Close-up view; male subject, age 30–39; the leg is involved:
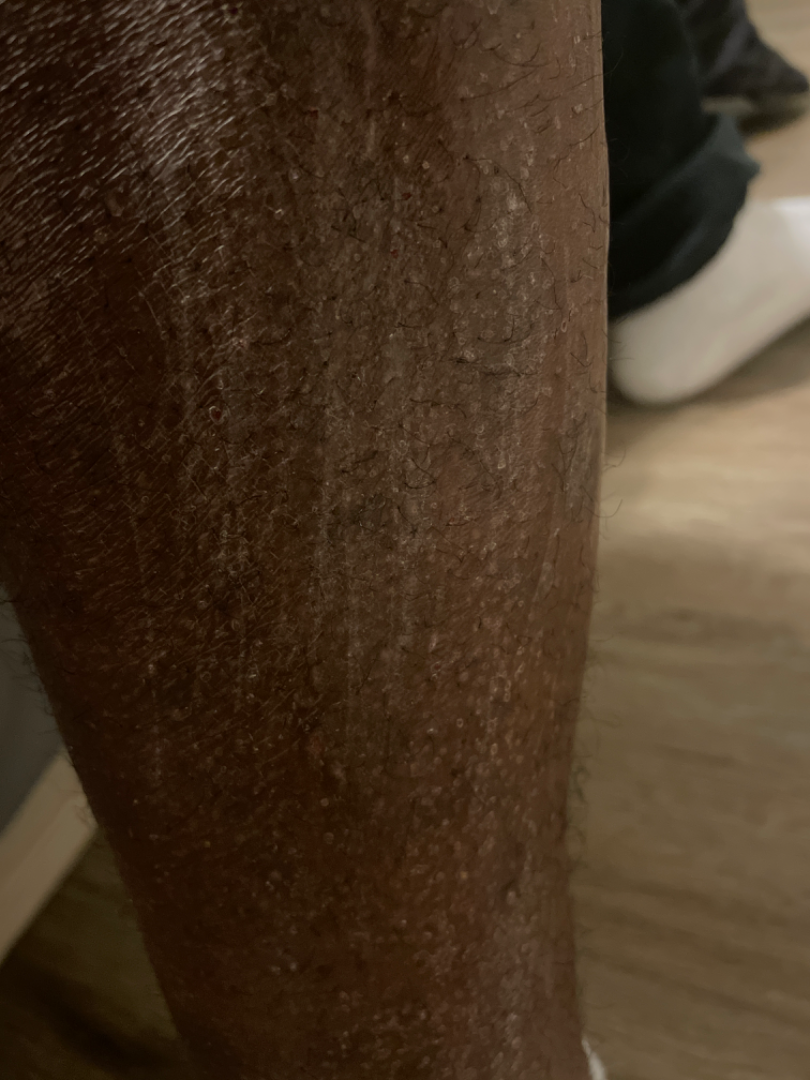Q: What was the assessment?
A: indeterminate from the photograph
Q: Texture?
A: rough or flaky
Q: How long has this been present?
A: one to four weeks
Q: Constitutional symptoms?
A: none reported